This image was taken at an angle.
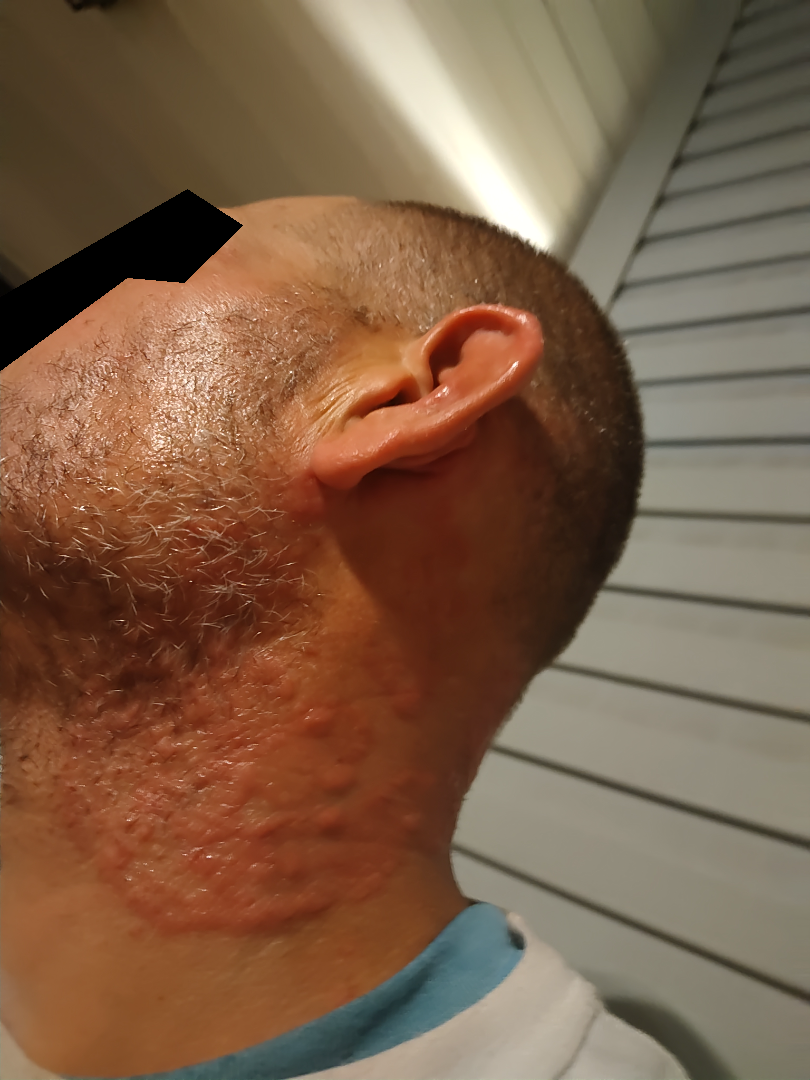Findings:
• assessment · Granuloma annulare (55%); Cutaneous sarcoidosis (27%); Erythema annulare centrifugum (18%)